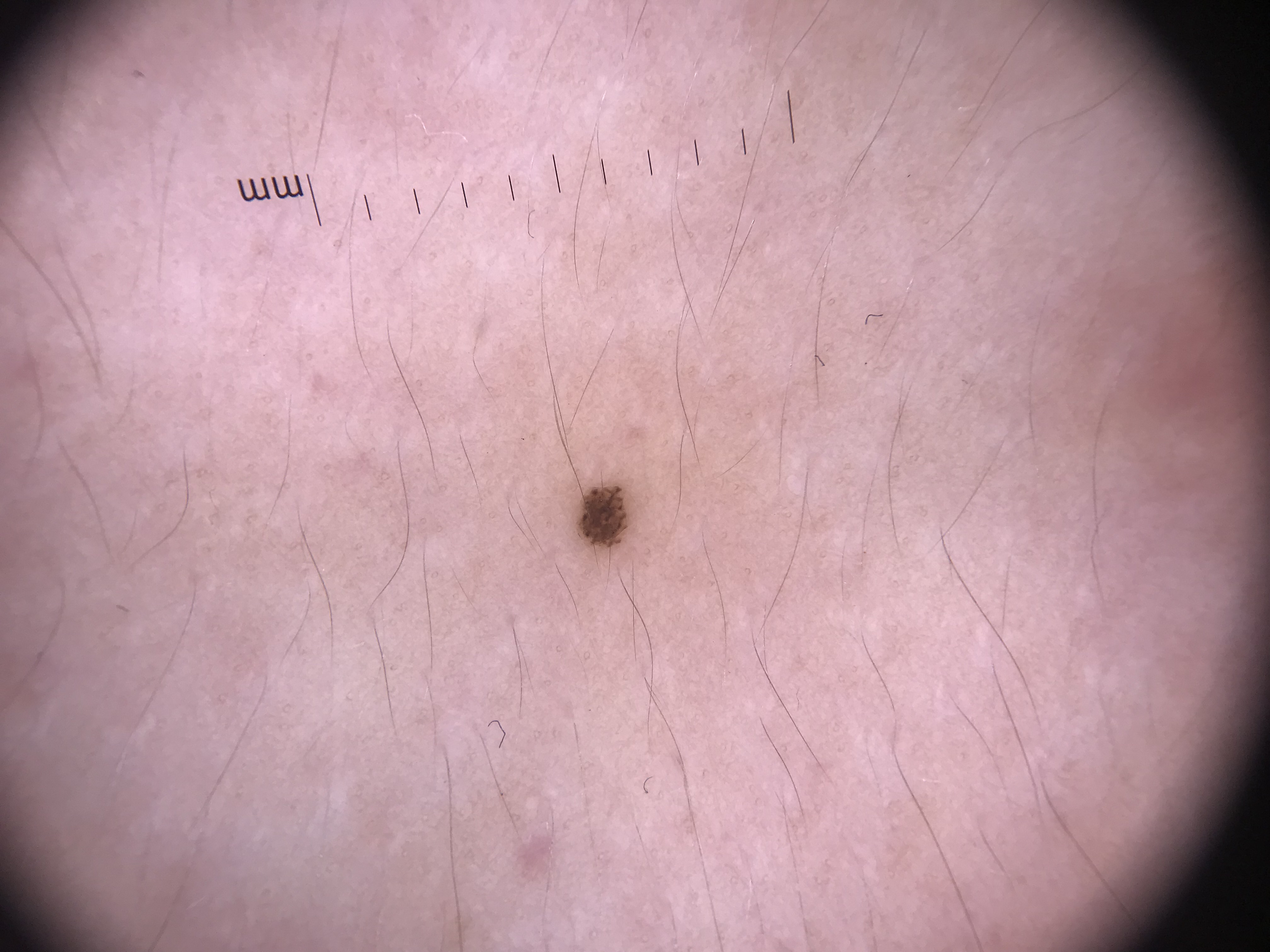A skin lesion imaged with a dermatoscope.
Consistent with a banal lesion — a junctional nevus.